A dermoscopic close-up of a skin lesion: 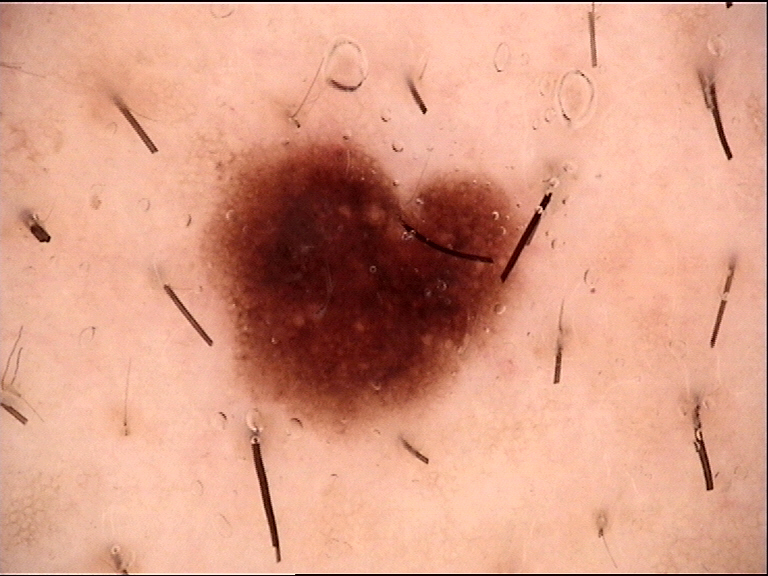| key | value |
|---|---|
| class | dysplastic junctional nevus (expert consensus) |